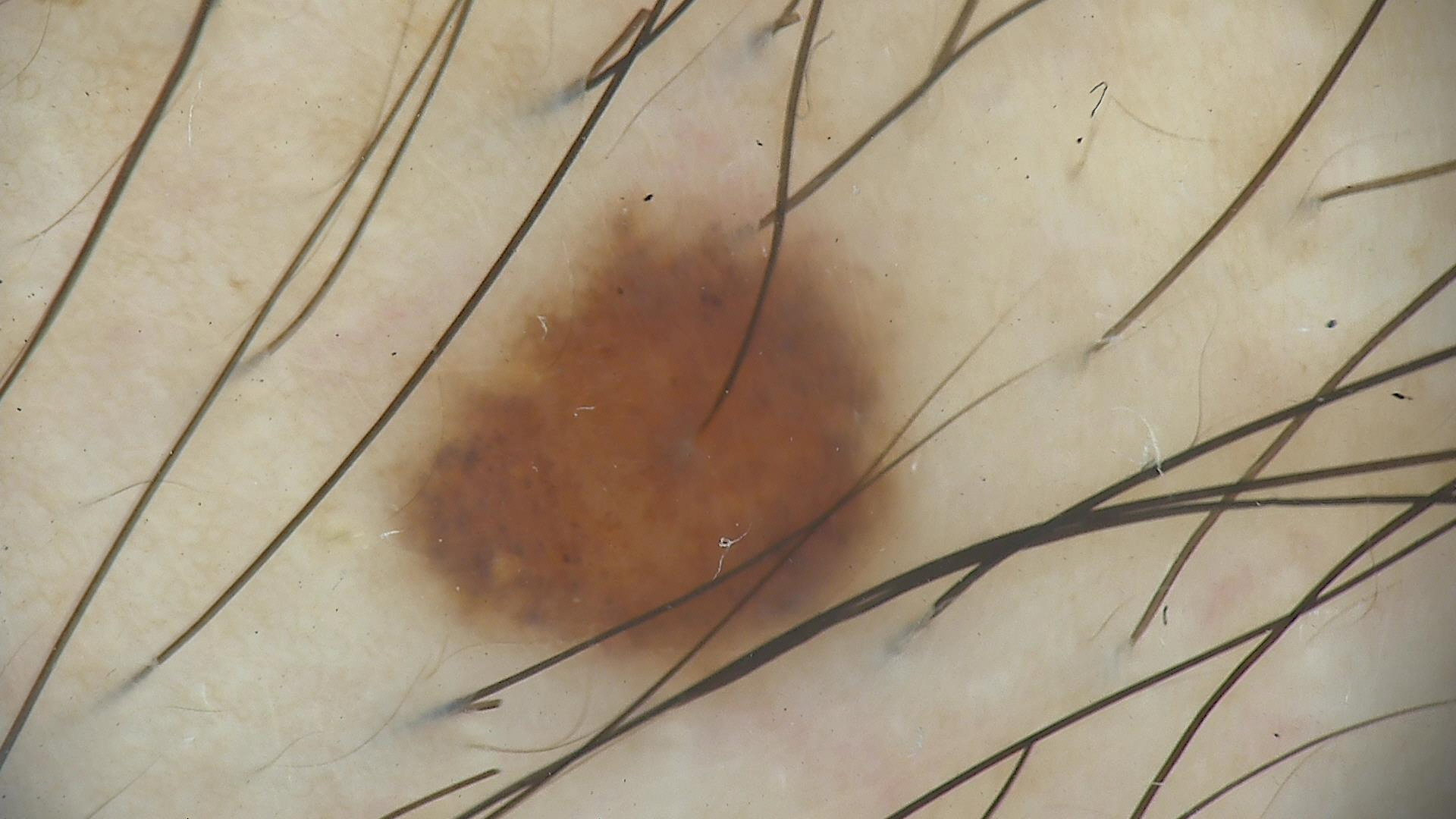Impression: Classified as a benign lesion — a dysplastic junctional nevus.